A close-up photograph. Located on the arm. The patient is male — 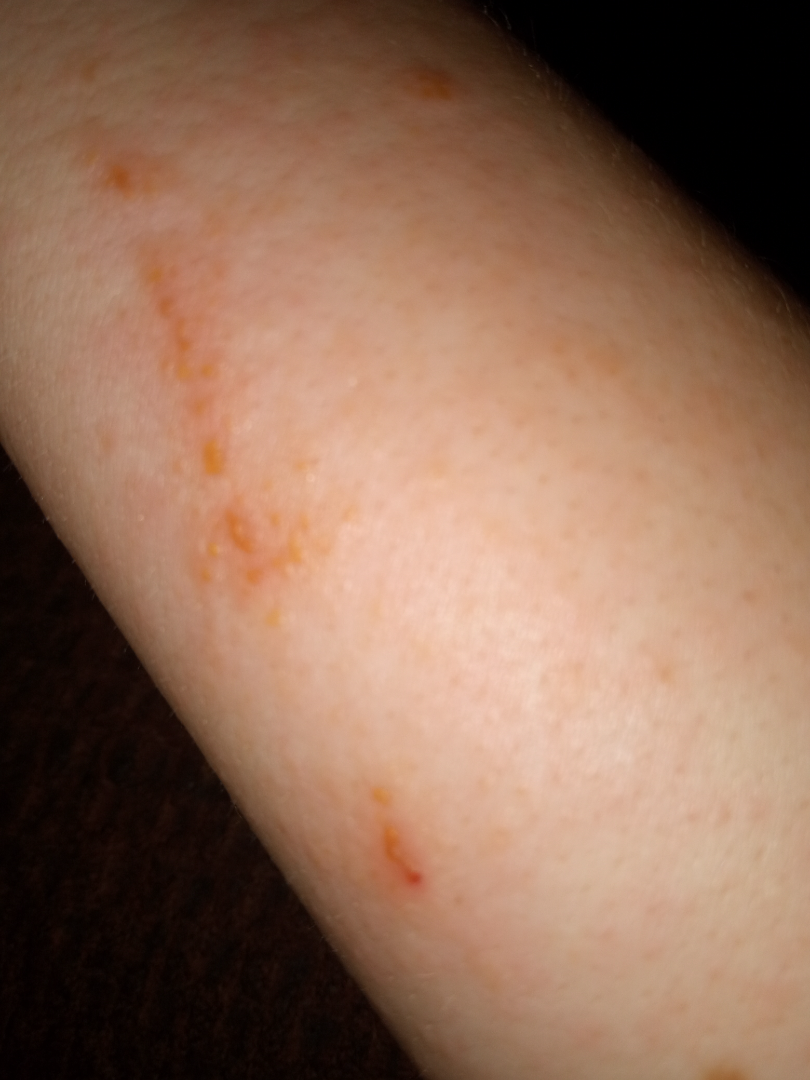Allergic Contact Dermatitis (most likely).